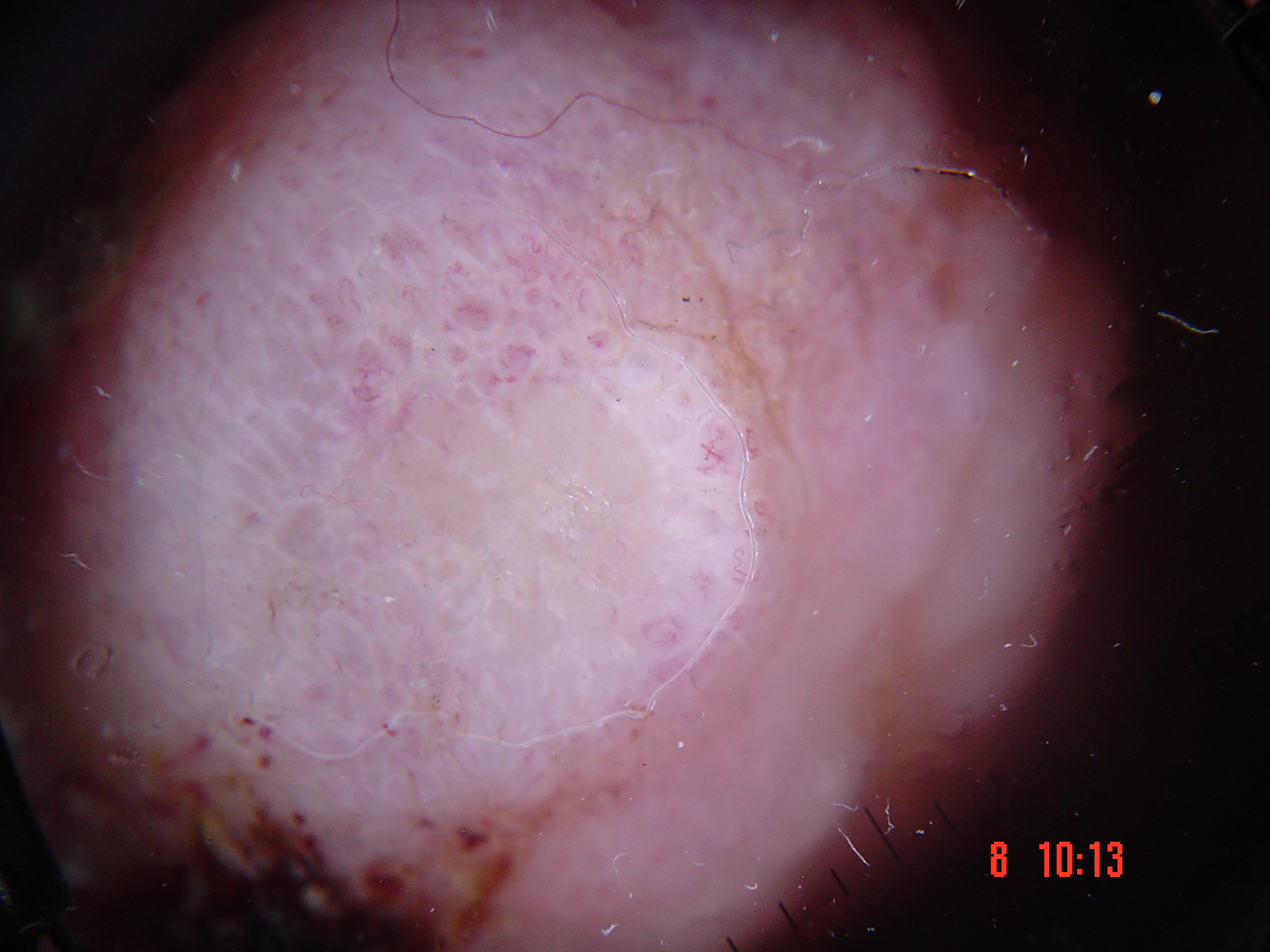{
  "image": "dermatoscopy",
  "diagnosis": {
    "name": "acral nodular melanoma",
    "code": "anm",
    "malignancy": "malignant",
    "super_class": "melanocytic",
    "confirmation": "histopathology"
  }
}